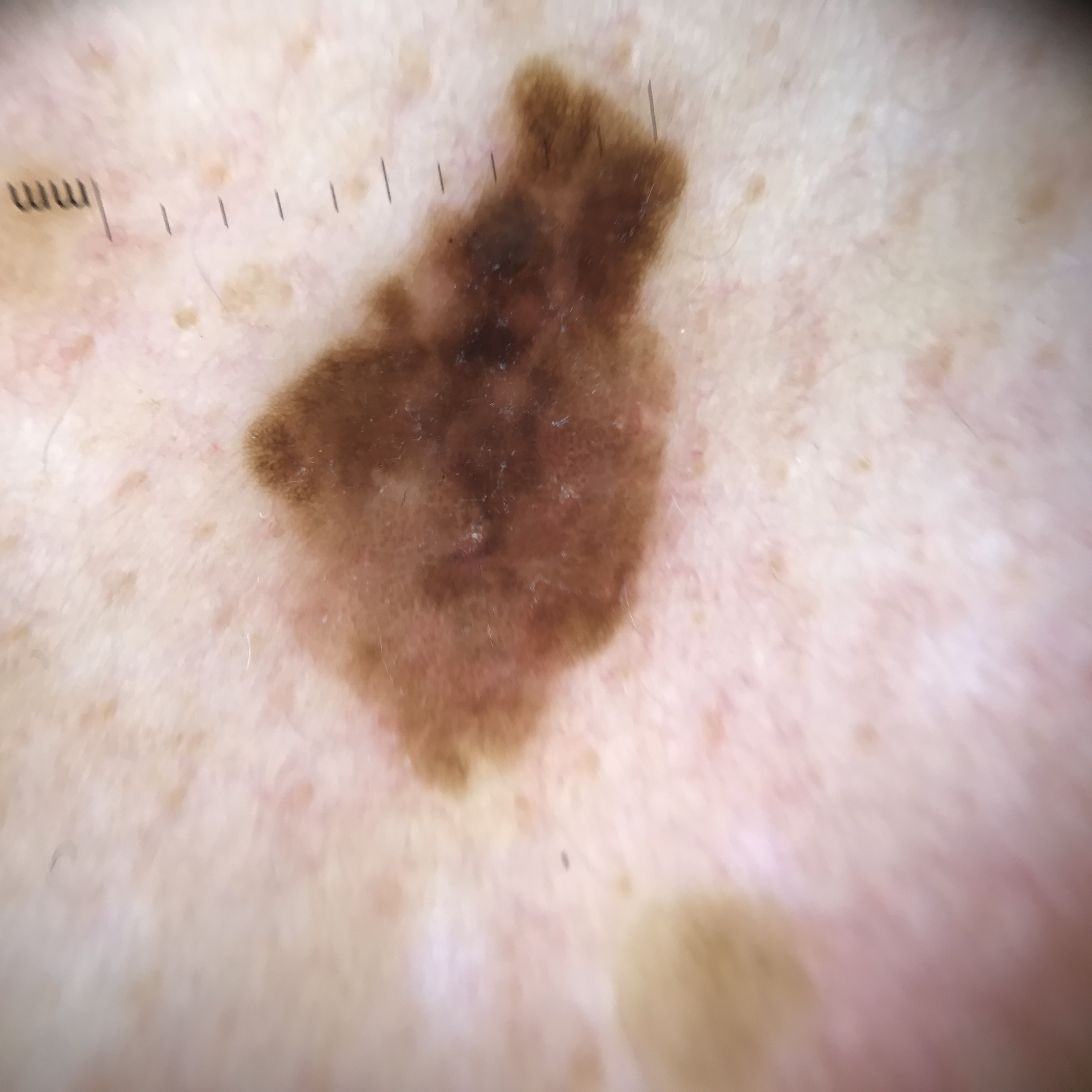  image: dermatoscopy
  diagnosis:
    name: melanoma
    code: mel
    malignancy: malignant
    super_class: melanocytic
    confirmation: histopathology